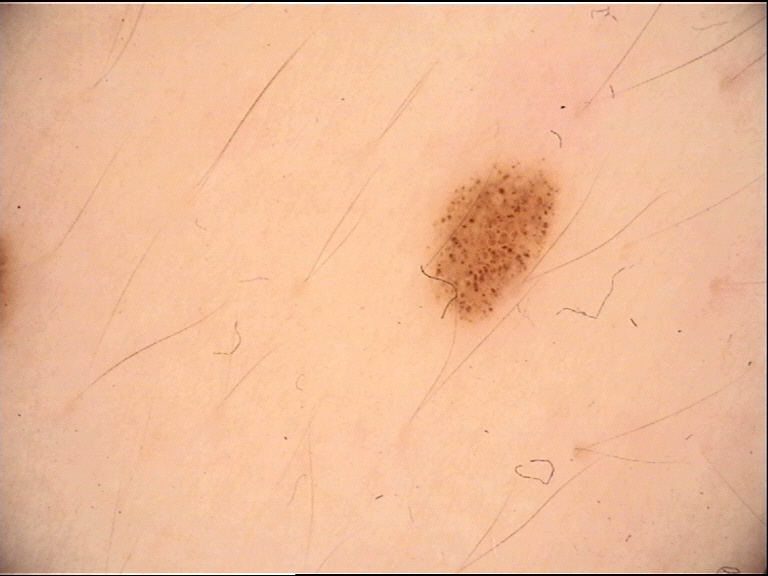A dermoscopic close-up of a skin lesion. Labeled as a dysplastic junctional nevus.